A dermoscopic close-up of a skin lesion:
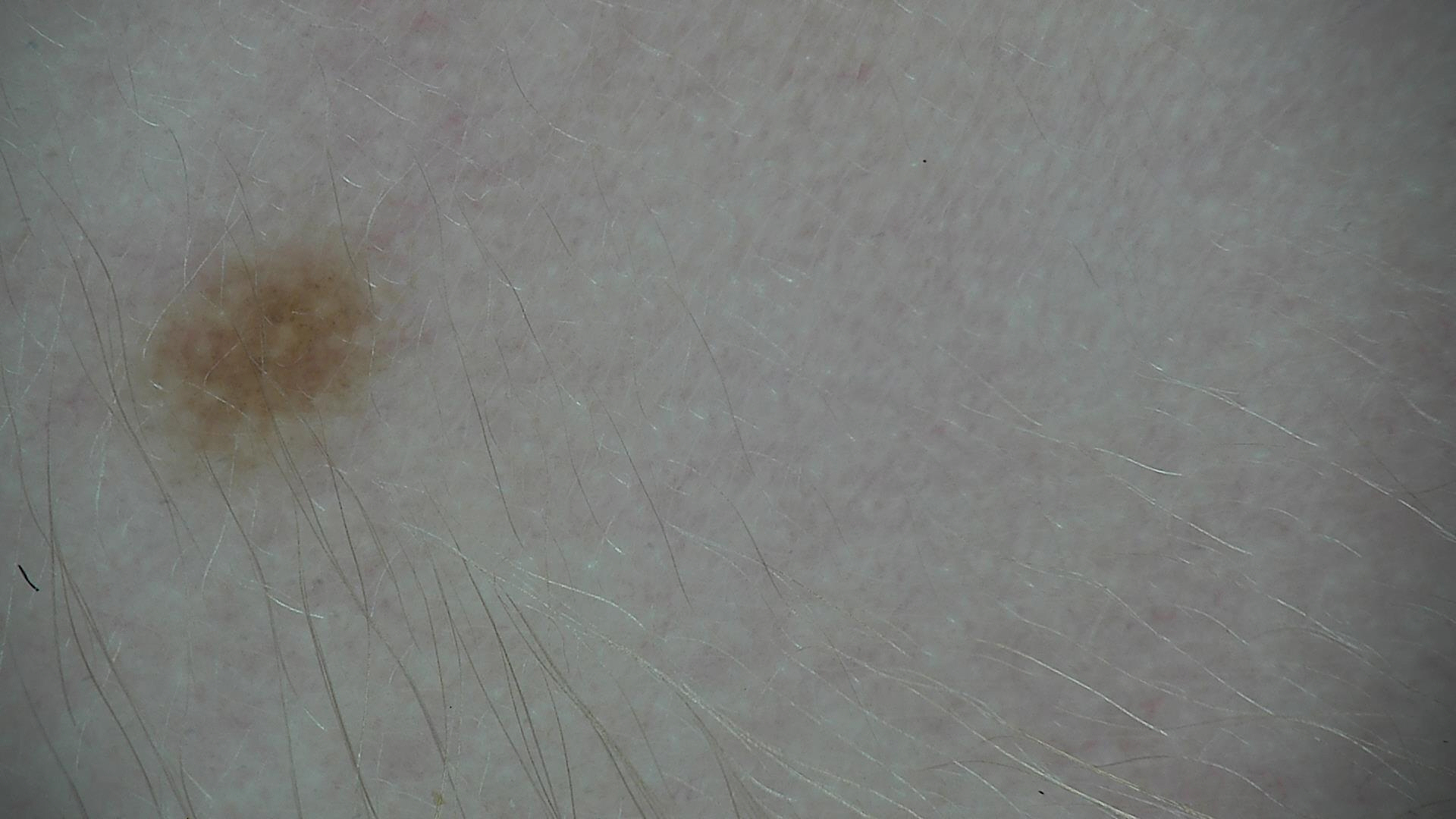• classification · banal, compound
• diagnosis · Miescher nevus (expert consensus)